A dermoscopic image of a skin lesion: 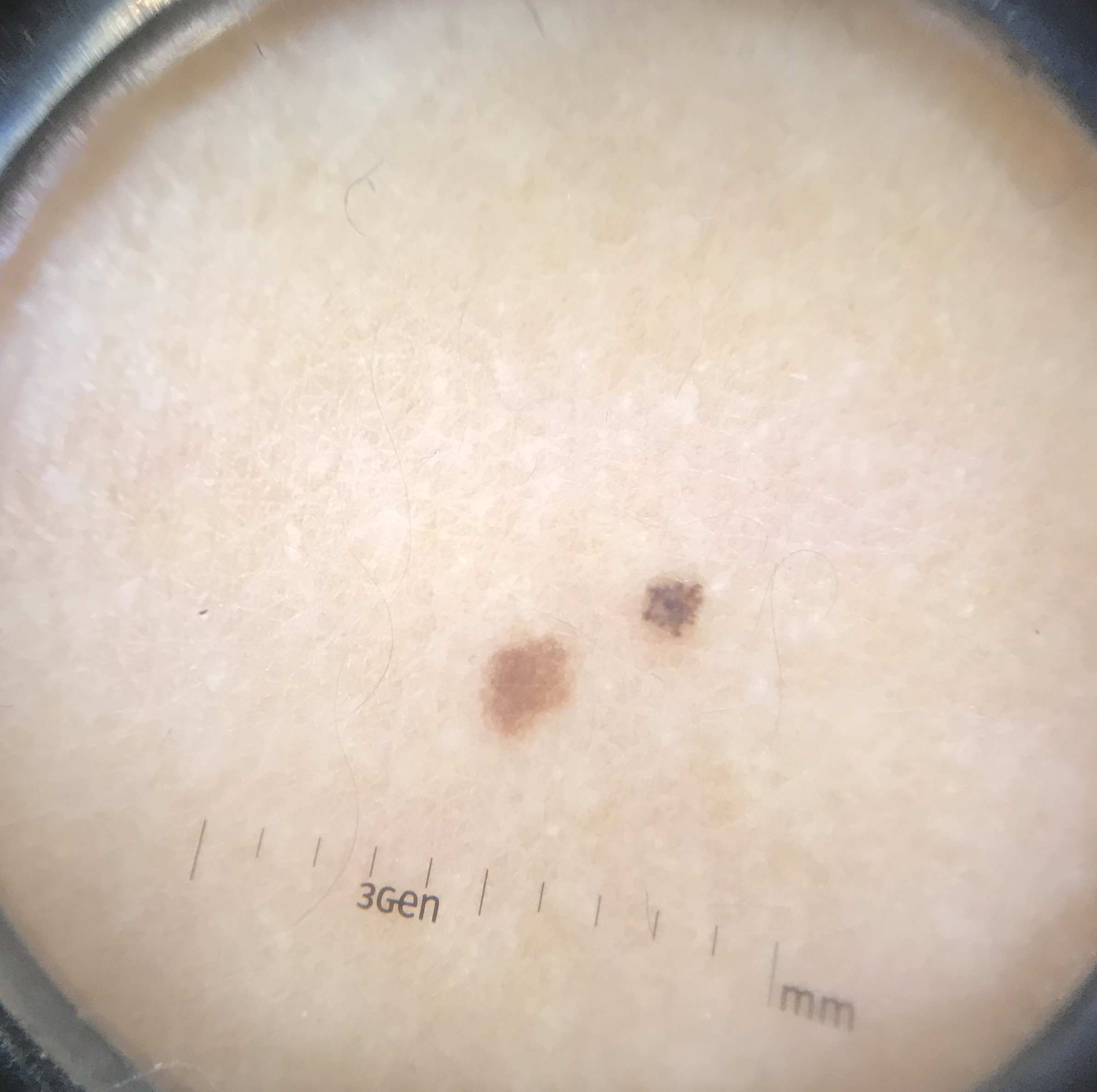* diagnosis — dysplastic junctional nevus (expert consensus)